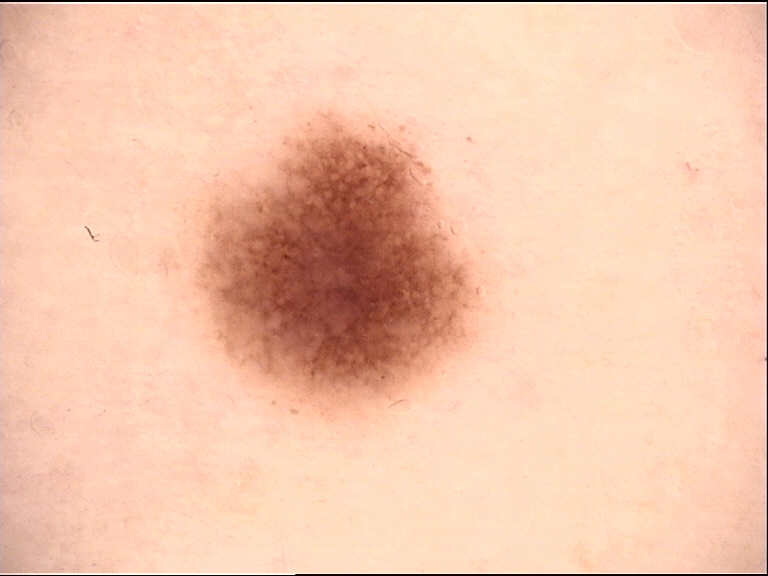Dermoscopy of a skin lesion. The diagnosis was a benign lesion — a dysplastic junctional nevus.